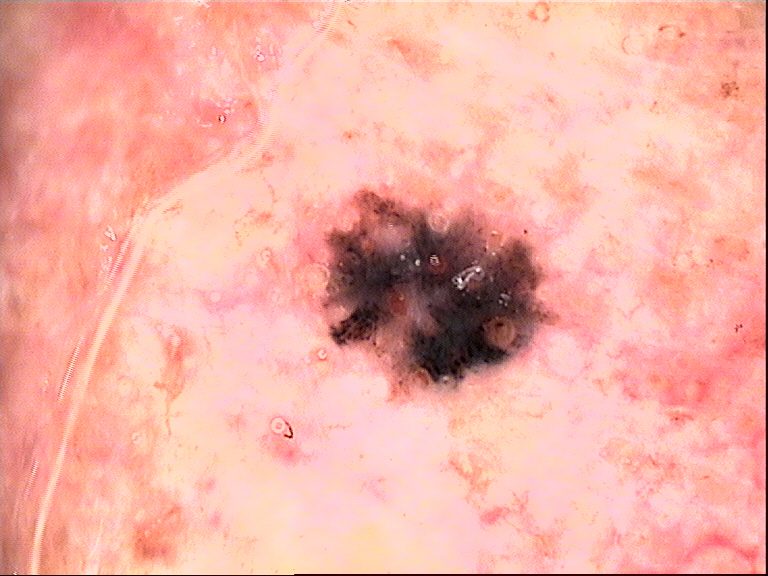Conclusion:
Confirmed on histopathology as a basal cell carcinoma.